A skin lesion imaged with a dermatoscope · a male subject roughly 75 years of age:
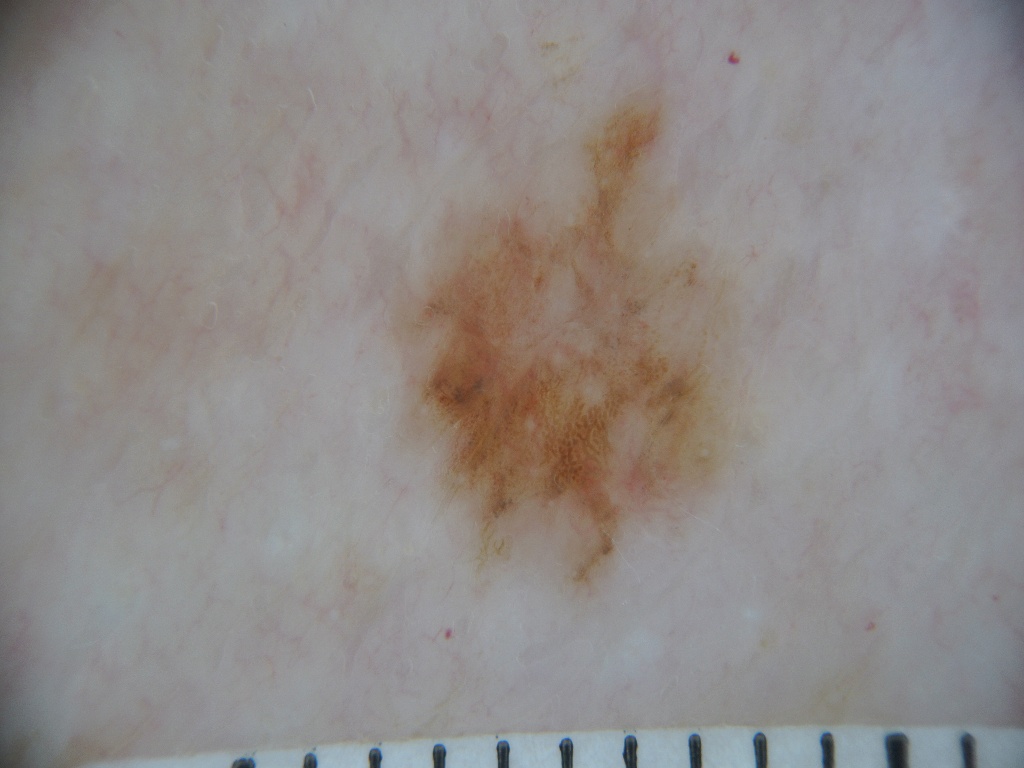The lesion occupies roughly 14% of the field. The dermoscopic pattern shows no globules, streaks, negative network, pigment network, or milia-like cysts. The lesion spans box(389, 82, 739, 595). Histopathologically confirmed as a melanoma, a malignant lesion.